The lesion involves the back of the hand, no associated systemic symptoms reported, texture is reported as raised or bumpy, skin tone: FST II, reported duration is one to four weeks, the contributor notes itching and burning, self-categorized by the patient as a rash, the photograph was taken at a distance.
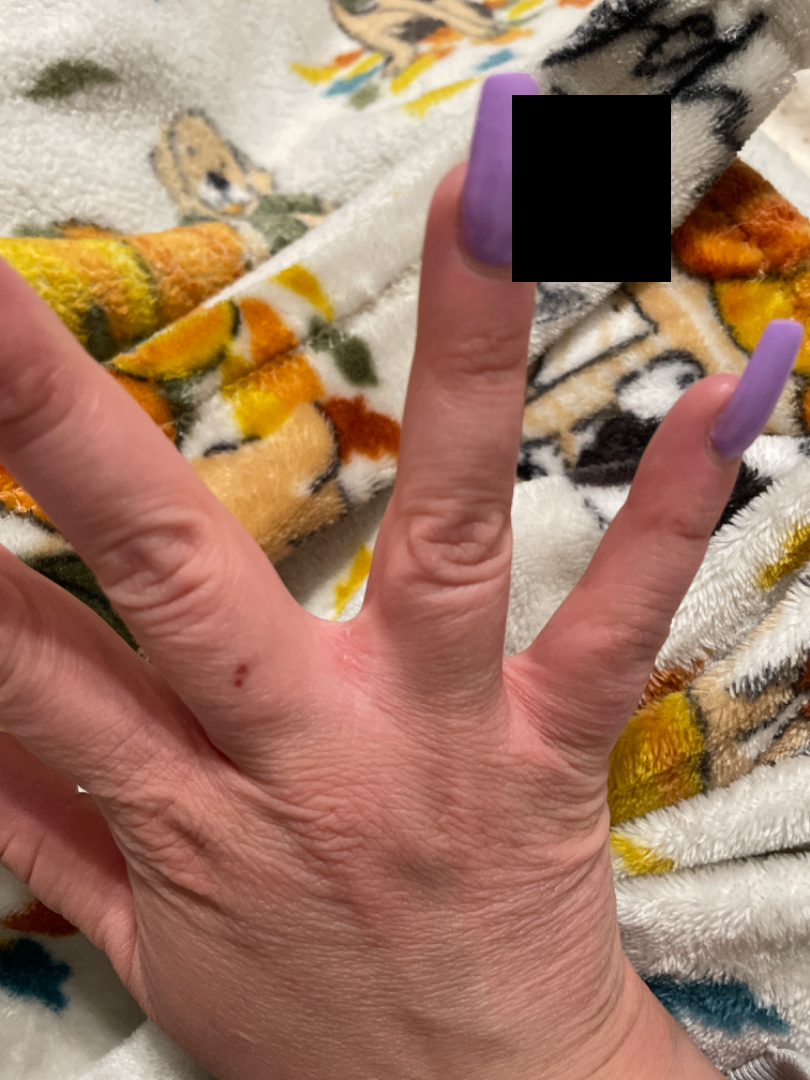Q: What conditions are considered?
A: single-reviewer assessment: consistent with Irritant Contact Dermatitis